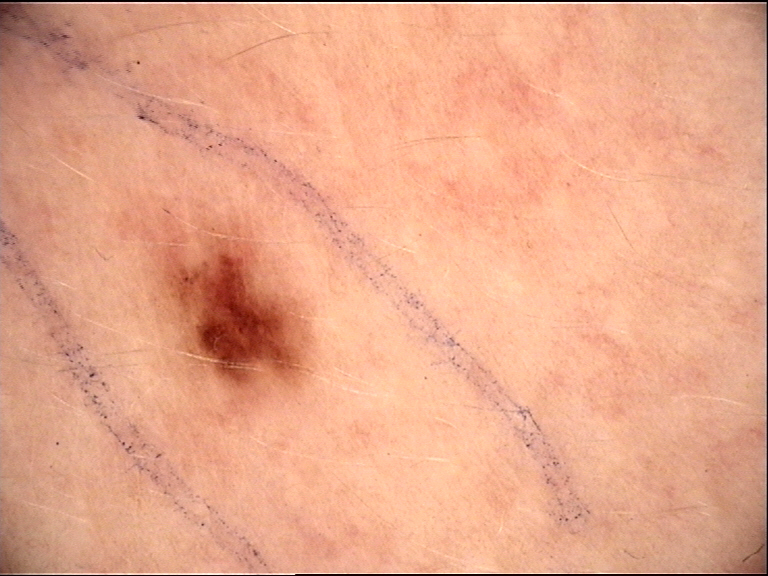The diagnostic label was a dysplastic junctional nevus.